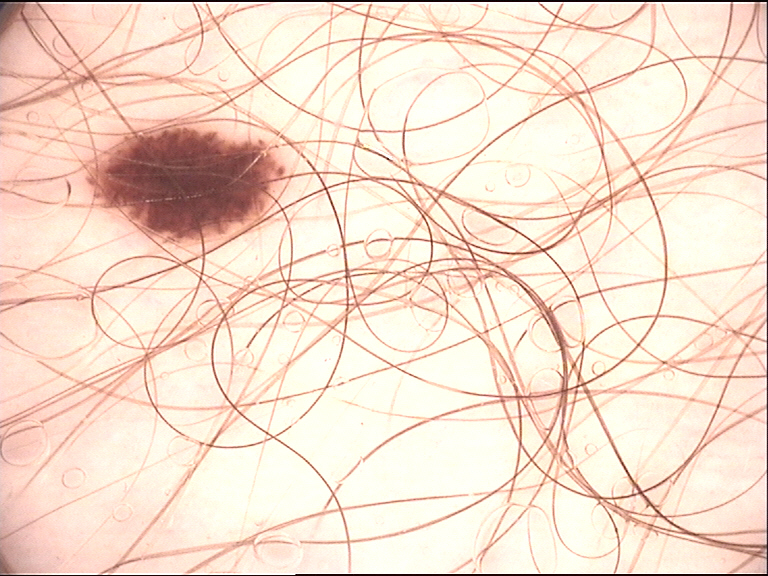{"diagnosis": {"name": "dysplastic junctional nevus", "code": "jd", "malignancy": "benign", "super_class": "melanocytic", "confirmation": "expert consensus"}}